A dermoscopic image of a skin lesion: 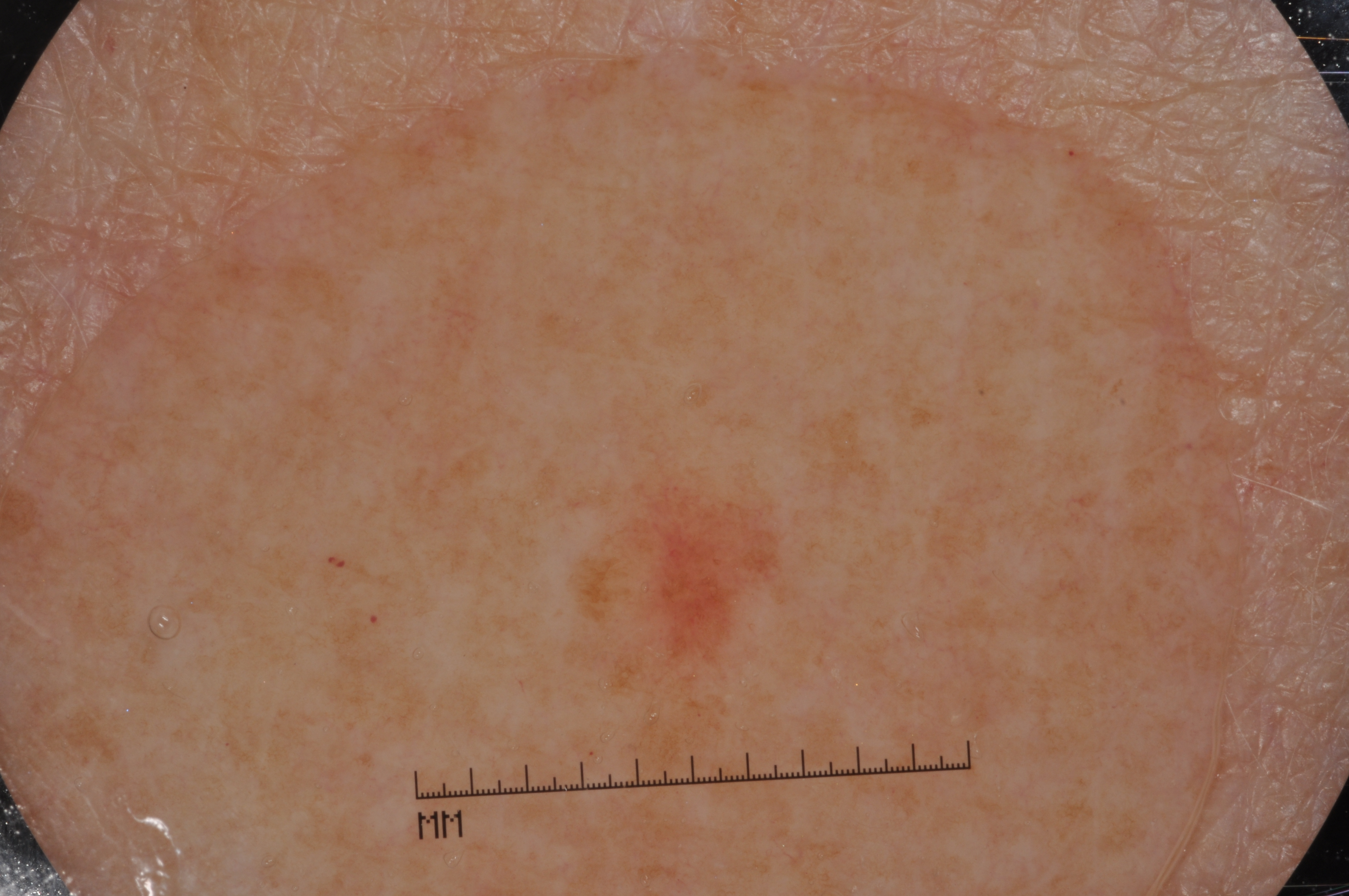{"lesion_location": {"bbox_xyxy": [558, 457, 798, 734]}, "lesion_extent": "small", "dermoscopic_features": {"present": [], "absent": ["milia-like cysts", "pigment network", "streaks", "negative network"]}, "diagnosis": {"name": "melanocytic nevus", "malignancy": "benign", "lineage": "melanocytic", "provenance": "clinical"}}